The subject is a female aged 18–29, close-up view, located on the arm: 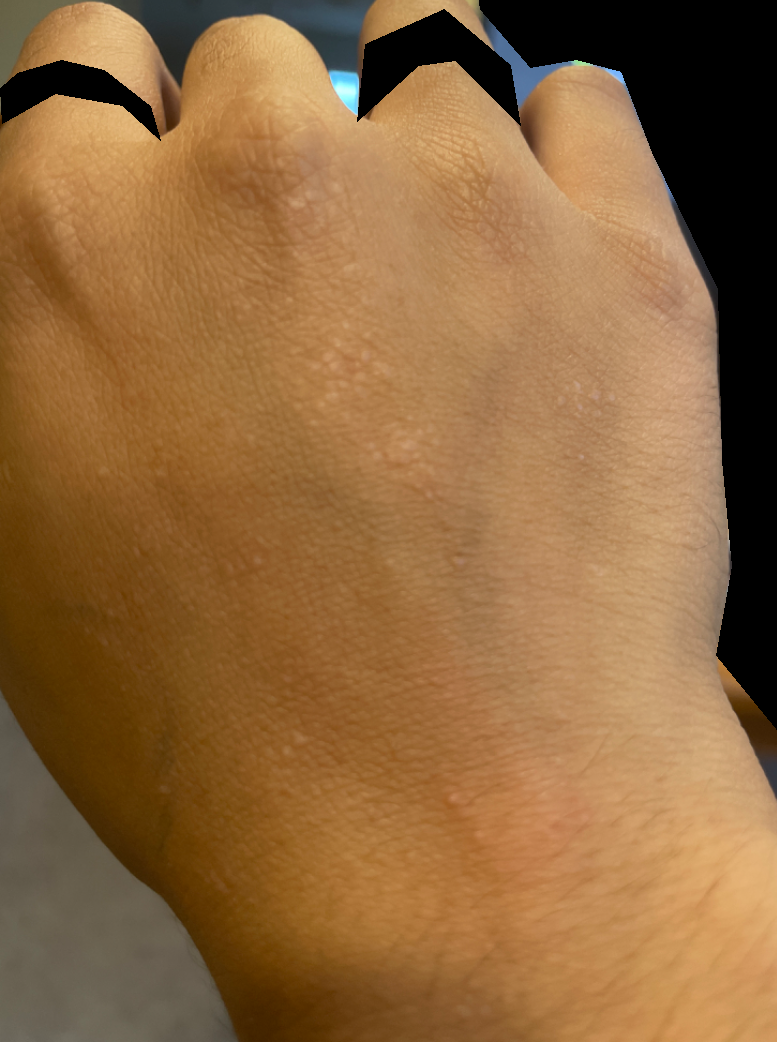Q: Fitzpatrick or Monk tone?
A: Fitzpatrick skin type IV
Q: Patient's own categorization?
A: a rash
Q: What symptoms does the patient report?
A: none reported
Q: What is the lesion texture?
A: flat
Q: Constitutional symptoms?
A: none reported
Q: What is the differential diagnosis?
A: Verruca vulgaris and Lichen planus/lichenoid eruption were considered with similar weight; lower on the differential is Lichen nitidus; a more distant consideration is Skin hypopigmented; less likely is Chronic dermatitis, NOS; less probable is Eczema